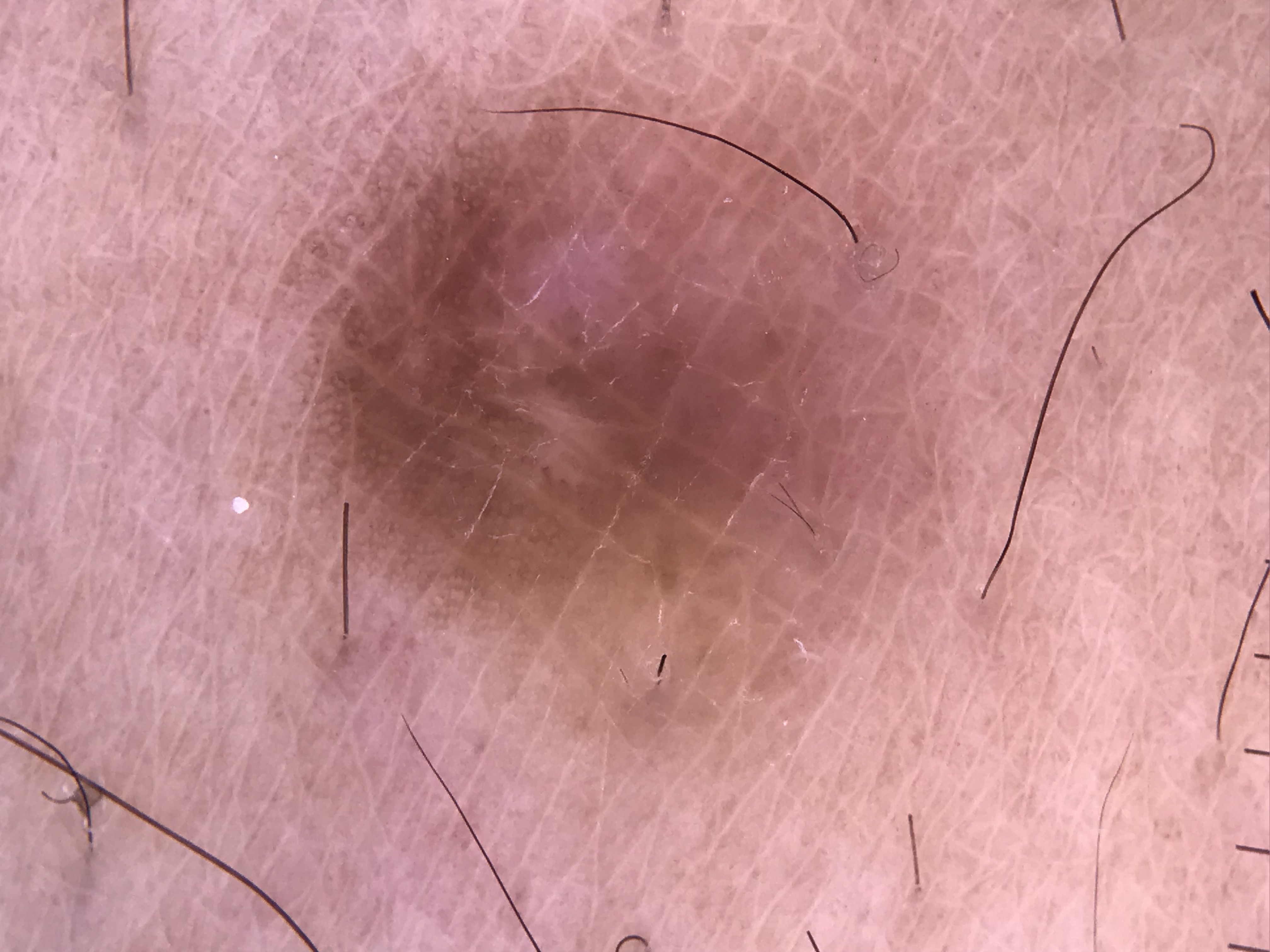Summary: The architecture is that of a fibro-histiocytic lesion. Impression: The diagnosis was a dermatofibroma.